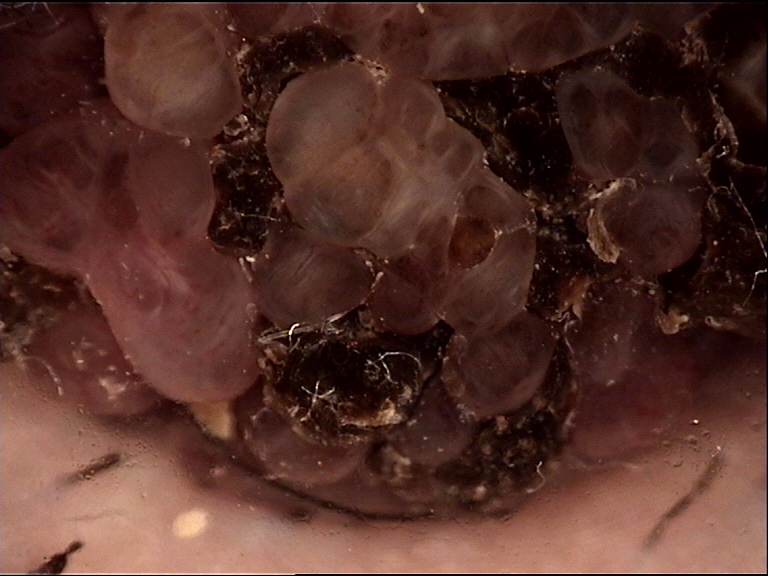assessment=congenital compound nevus (expert consensus).